The subject is a female aged 60–69. The patient also reports chills. Self-categorized by the patient as a rash. Located on the arm. Symptoms reported: itching, enlargement and burning. The photograph was taken at an angle. Fitzpatrick phototype II. The patient indicates the condition has been present for less than one week.
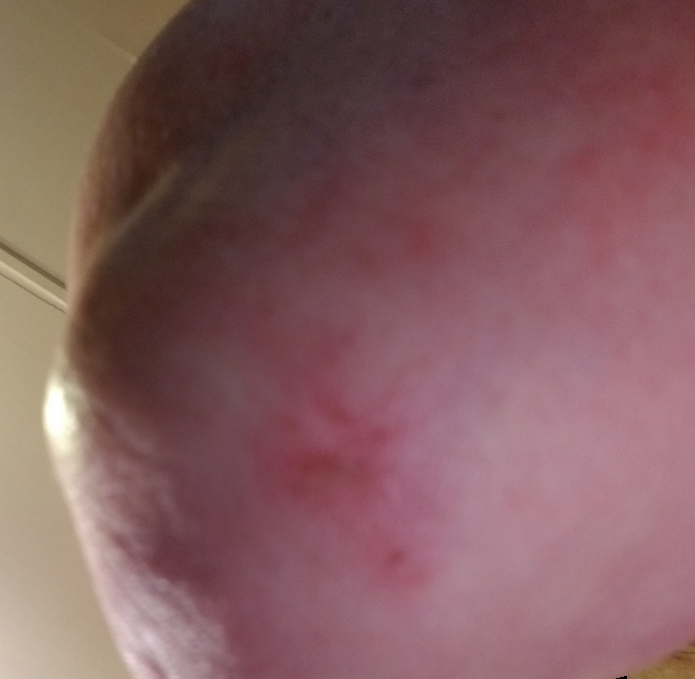Q: Could the case be diagnosed?
A: unable to determine